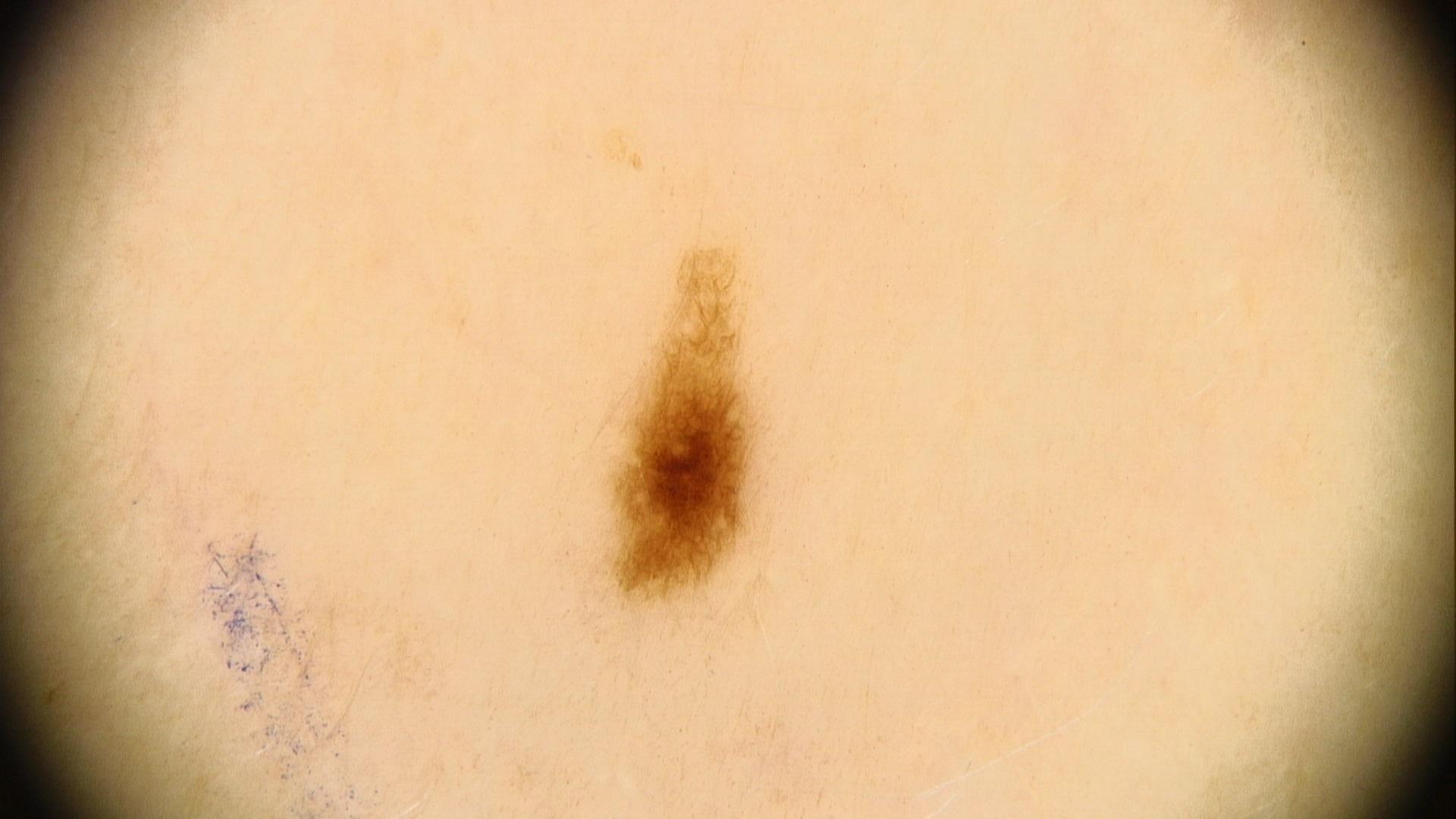melanoma_history:
  family_hx_melanoma: true
image: dermoscopy
patient:
  age_approx: 40
  sex: male
skin_type: III
lesion_location:
  region: the trunk
  detail: the anterior trunk
diagnosis:
  name: Nevus
  malignancy: benign
  confirmation: expert clinical impression
  lineage: melanocytic